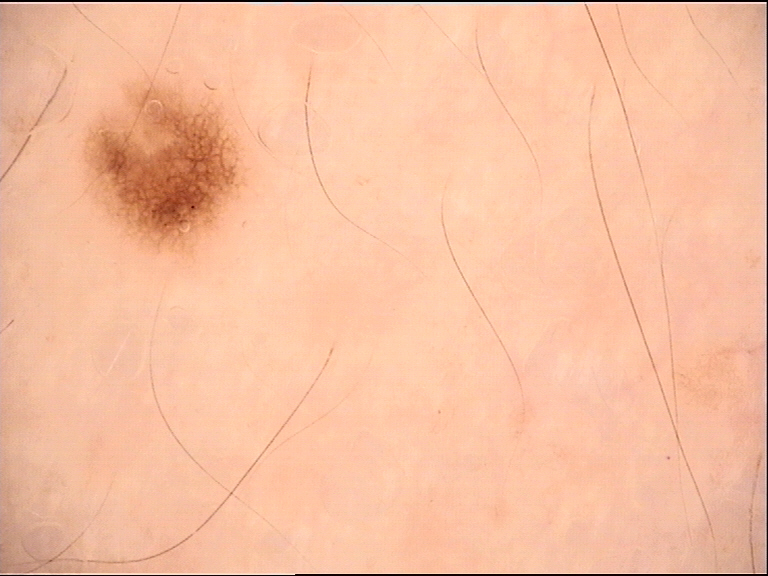A dermoscopy image of a single skin lesion. Labeled as a dysplastic junctional nevus.